The condition has been present for about one day. This image was taken at a distance. Fitzpatrick skin type III. Reported lesion symptoms include burning. The head or neck is involved. Self-categorized by the patient as a rash. The patient indicates the lesion is flat. No relevant systemic symptoms. The contributor is a female aged 40–49.
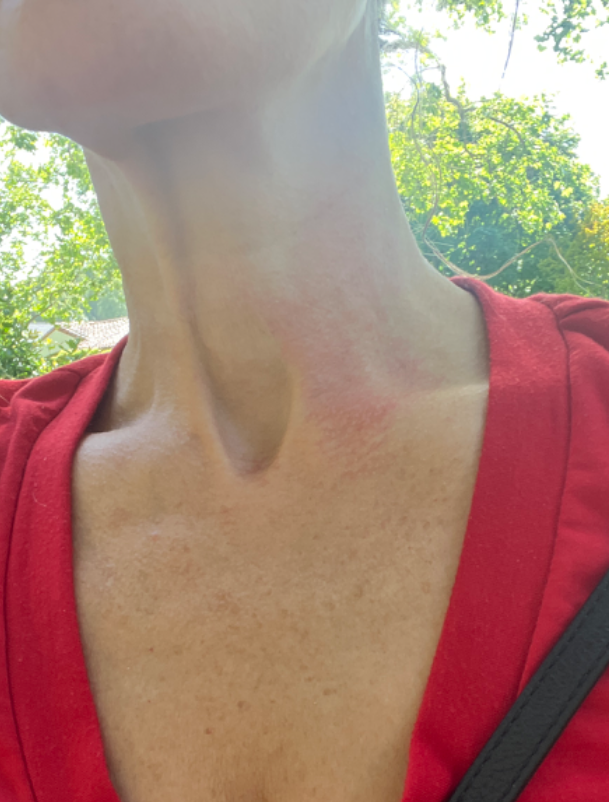{
  "differential": [
    "Allergic Contact Dermatitis",
    "Irritant Contact Dermatitis"
  ]
}